The subject is a male aged 30–39, an image taken at a distance, located on the leg:
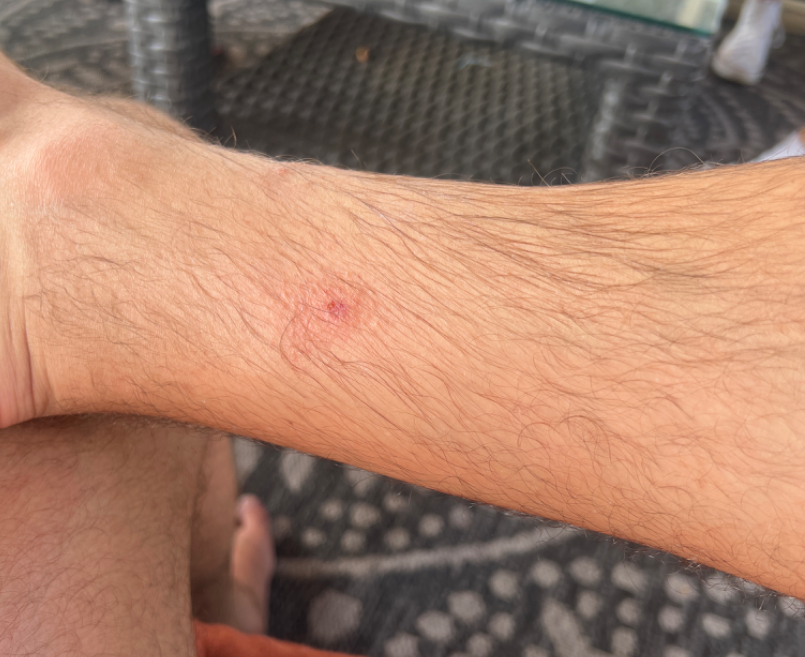differential: Insect Bite